A dermatoscopic image of a skin lesion: 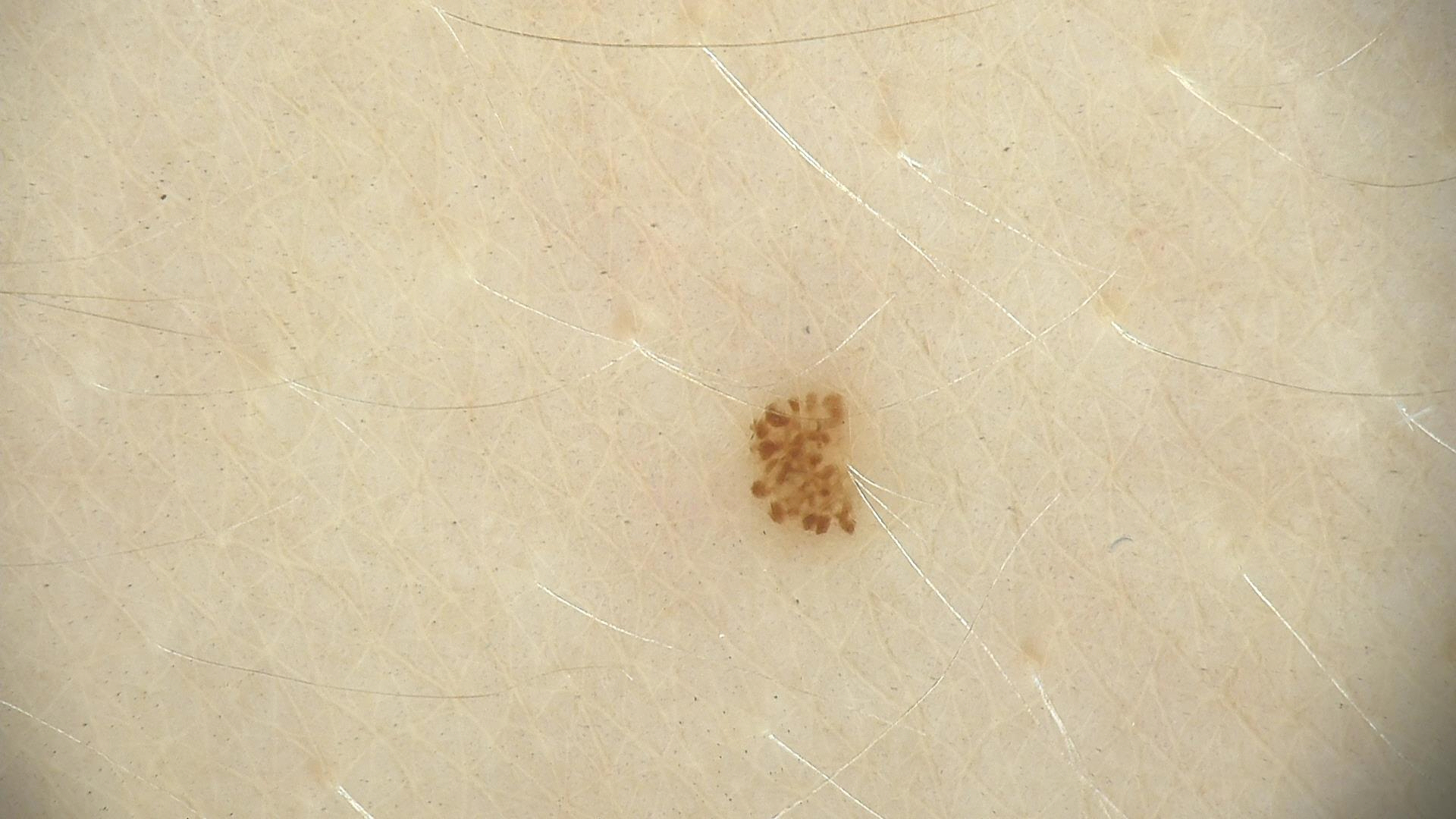The diagnosis was a benign lesion — a dysplastic junctional nevus.